The subject is a male roughly 85 years of age or older; a dermoscopic close-up of a skin lesion — 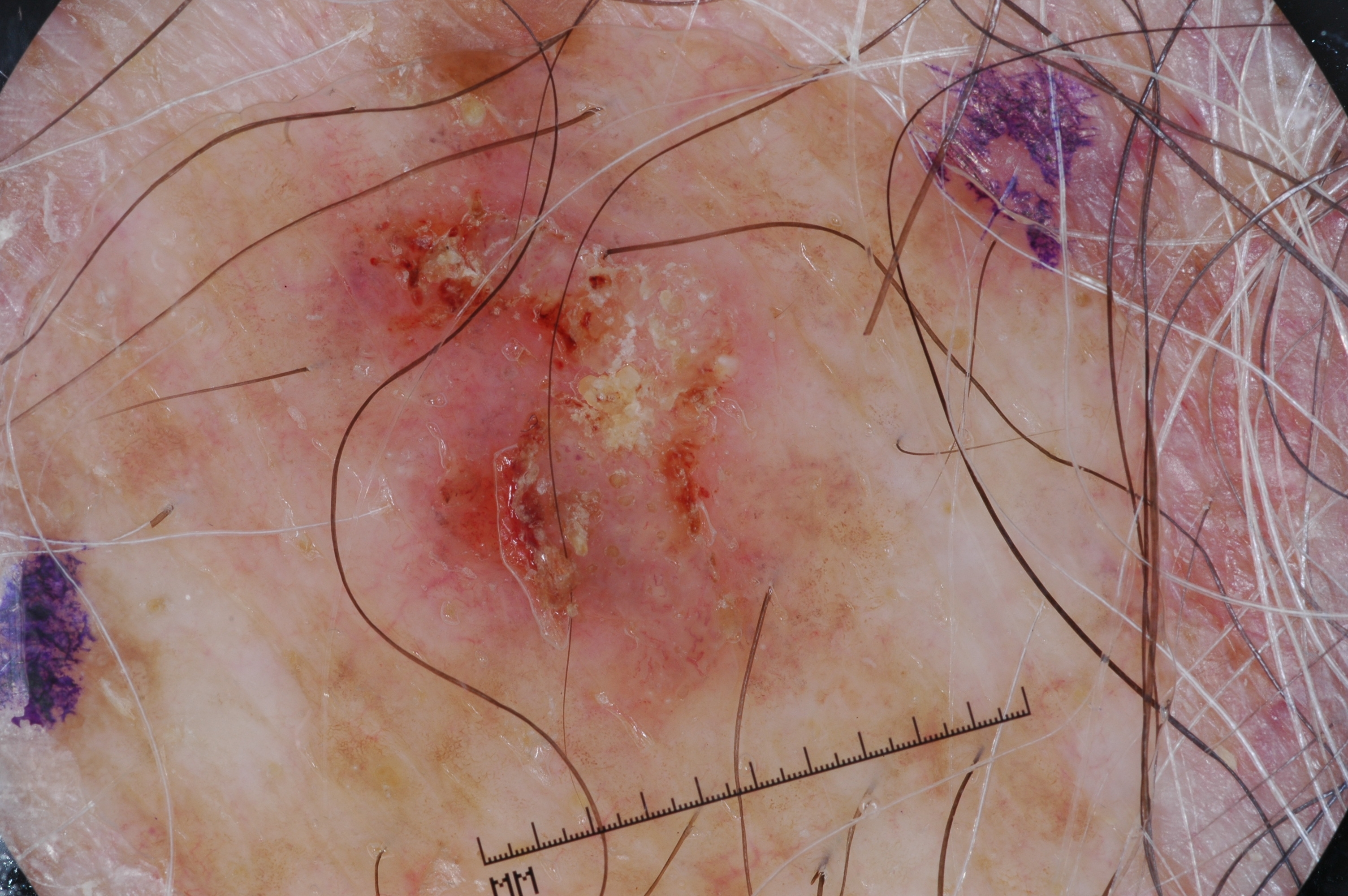lesion bbox = x1=283, y1=2, x2=919, y2=769
features = milia-like cysts
impression = a seborrheic keratosis